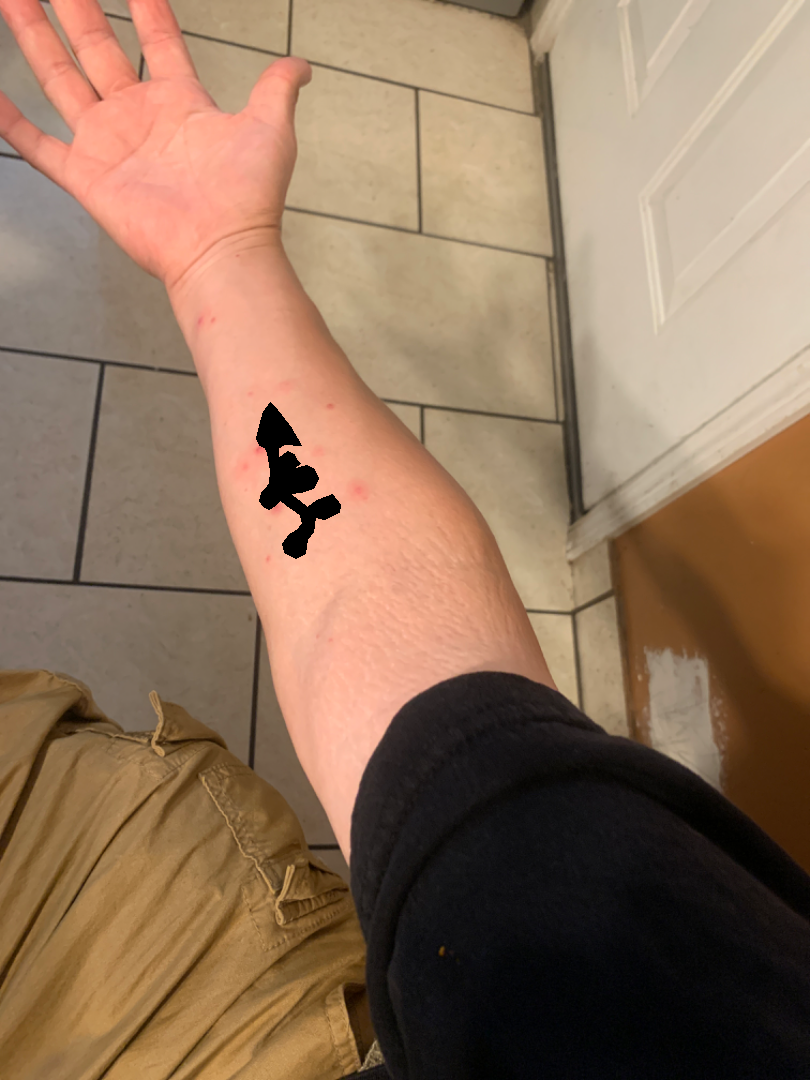location = arm | framing = at a distance | patient's own categorization = skin that appeared healthy to them | systemic symptoms = none reported | duration = one to four weeks | diagnostic considerations = most likely Insect Bite; an alternative is Eczema; possibly Allergic Contact Dermatitis.